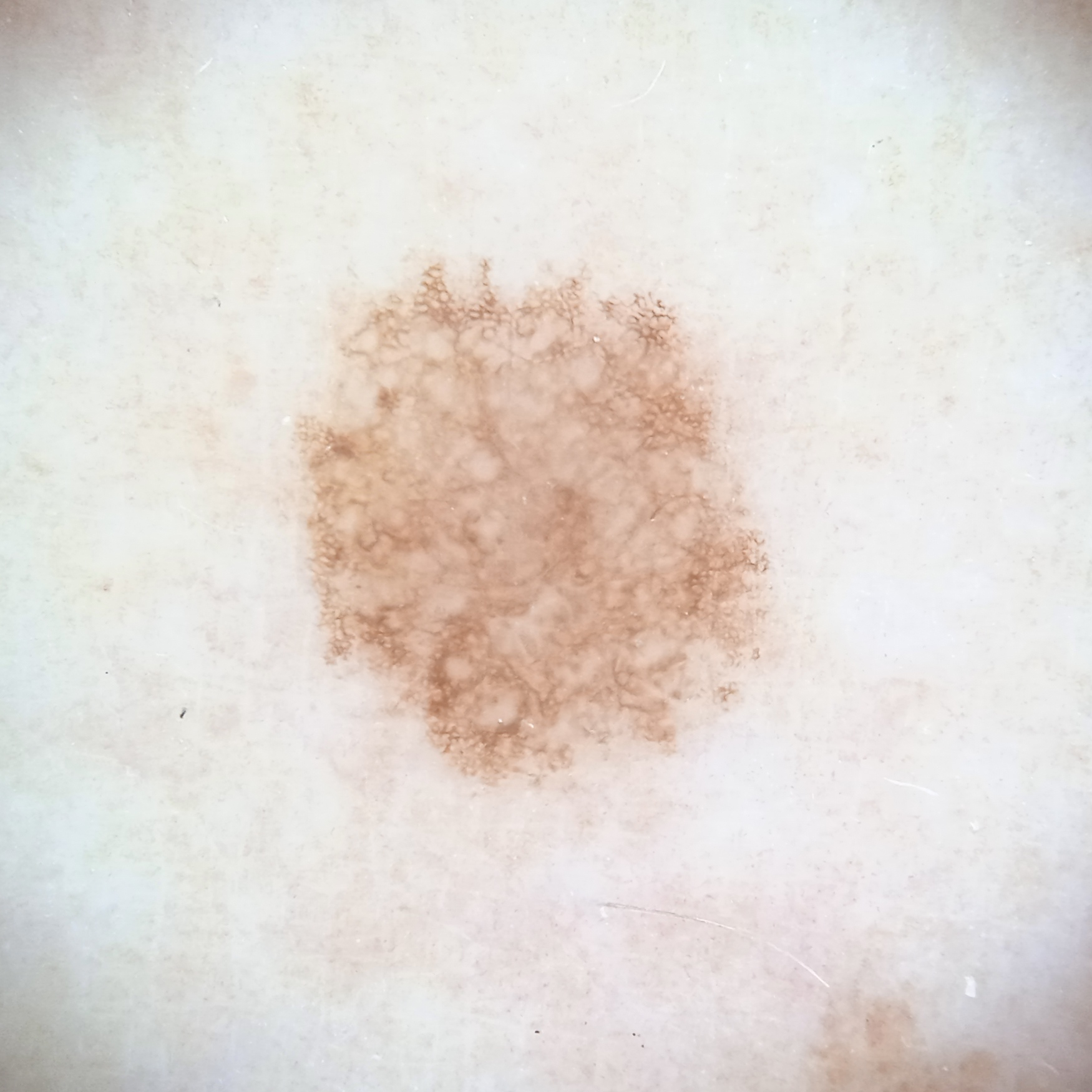modality: dermoscopic image | subject: female, 59 years of age | clinical context: clinical suspicion of melanocytic nevus | nevus count: a moderate number of melanocytic nevi | sun reaction: skin reddens with sun exposure | body site: an arm | lesion size: 6.7 mm | diagnostic label: atypical (dysplastic) nevus — biopsy-proven.